A skin lesion imaged with a dermatoscope.
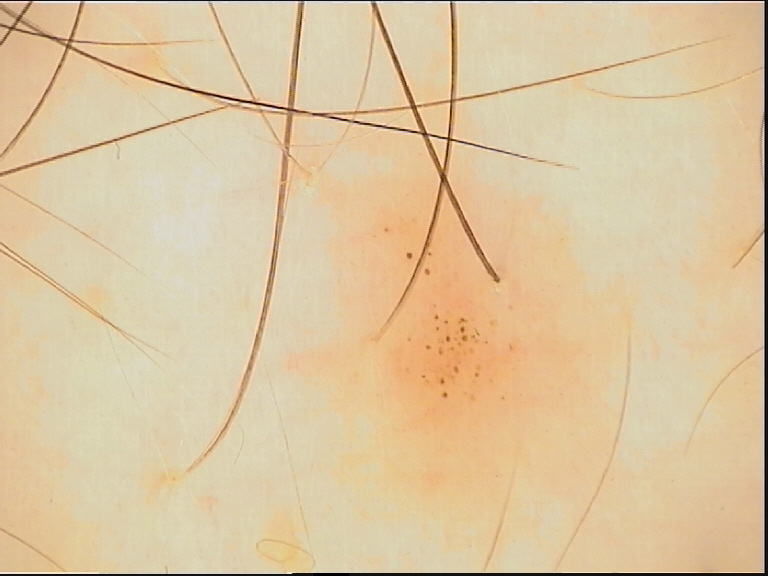Consistent with a banal lesion — a junctional nevus.